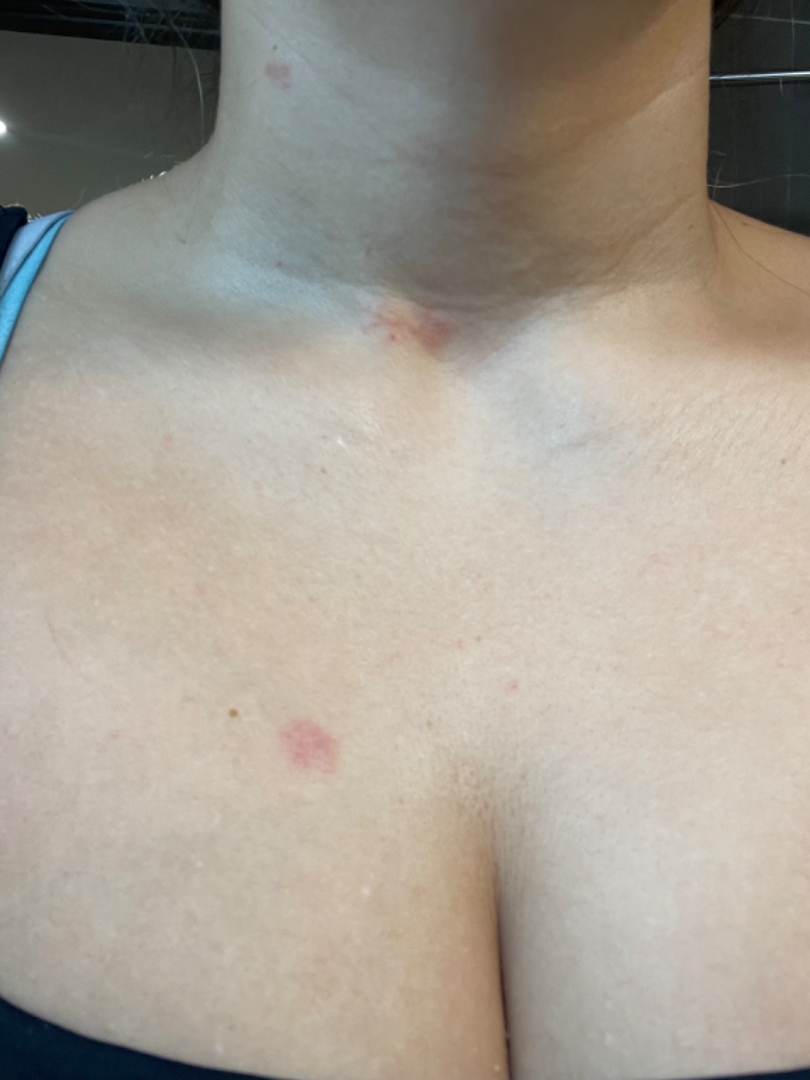On remote review of the image: Eczema (favored); Allergic Contact Dermatitis (possible); Tinea (possible); Contact dermatitis (remote).